The patient indicates the condition has been present for about one day; this image was taken at a distance; the patient reported no systemic symptoms; the lesion is described as raised or bumpy; symptoms reported: itching; the lesion involves the arm; the patient described the issue as skin that appeared healthy to them — 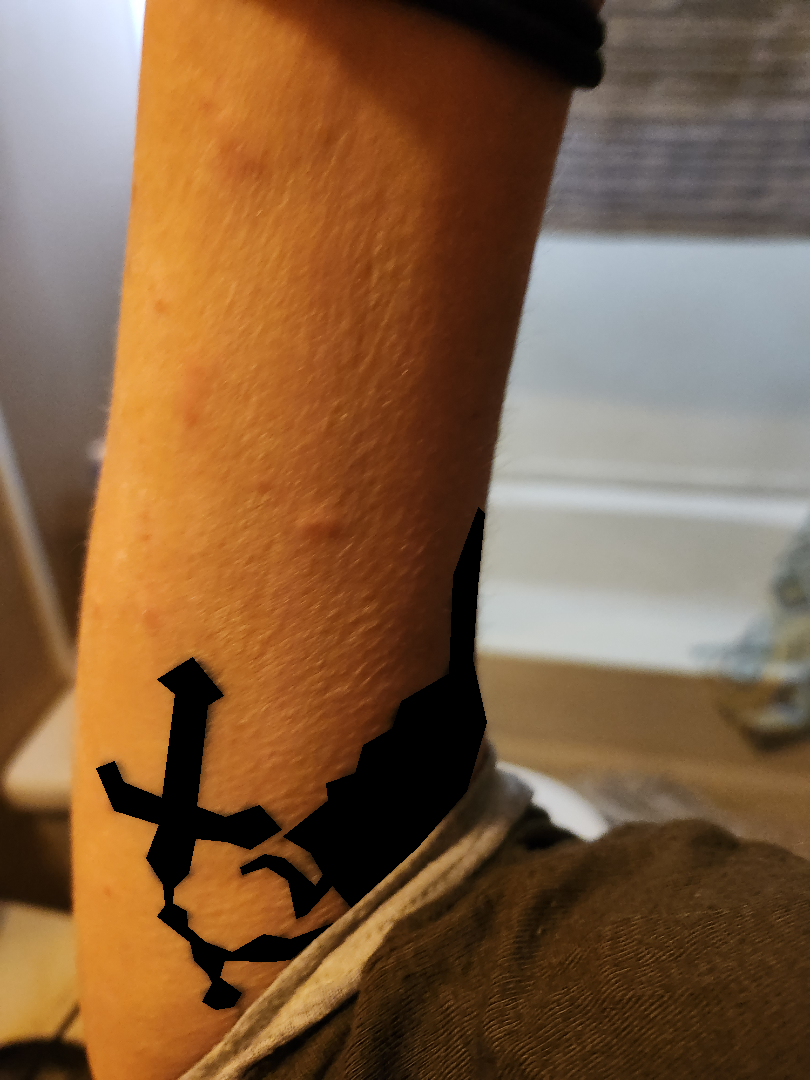{
  "assessment": "indeterminate"
}